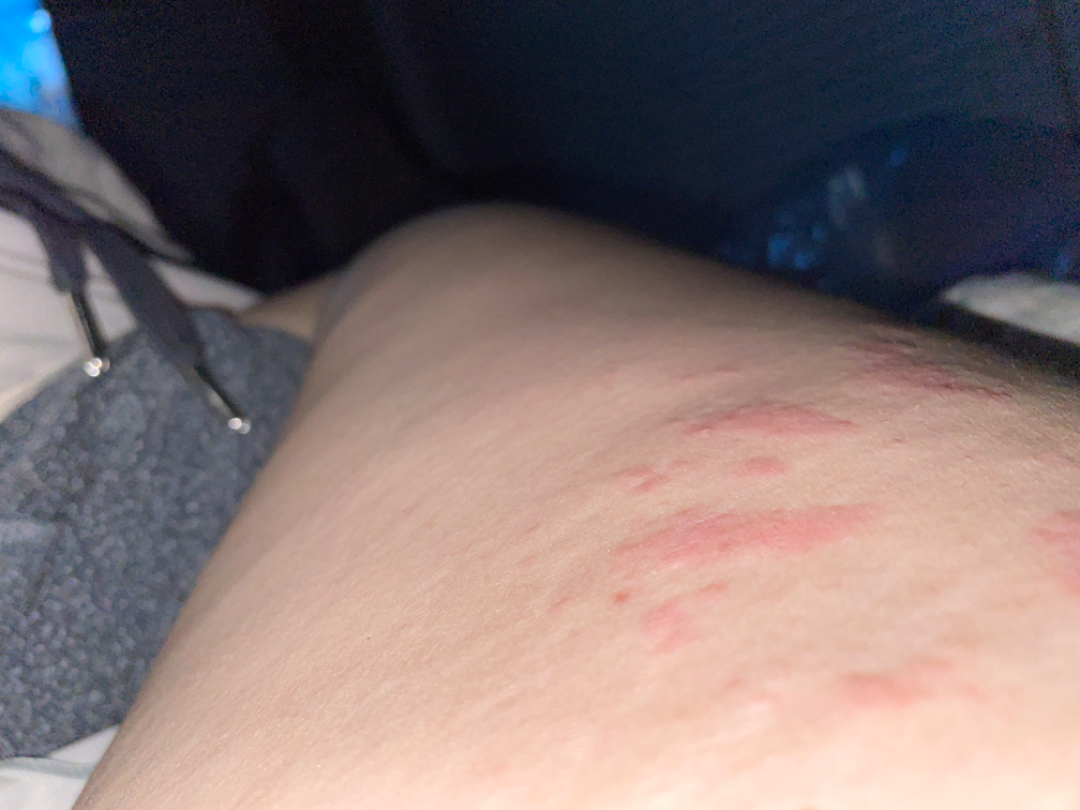Impression: The condition could not be reliably identified from the image. History: Texture is reported as raised or bumpy. The lesion involves the front of the torso, arm, back of the hand and head or neck. The photograph was taken at an angle. The patient also reports fatigue and joint pain. The patient described the issue as a rash. The contributor notes the condition has been present for less than one week. The lesion is associated with burning, pain, enlargement and itching. The contributor is a female aged 30–39.